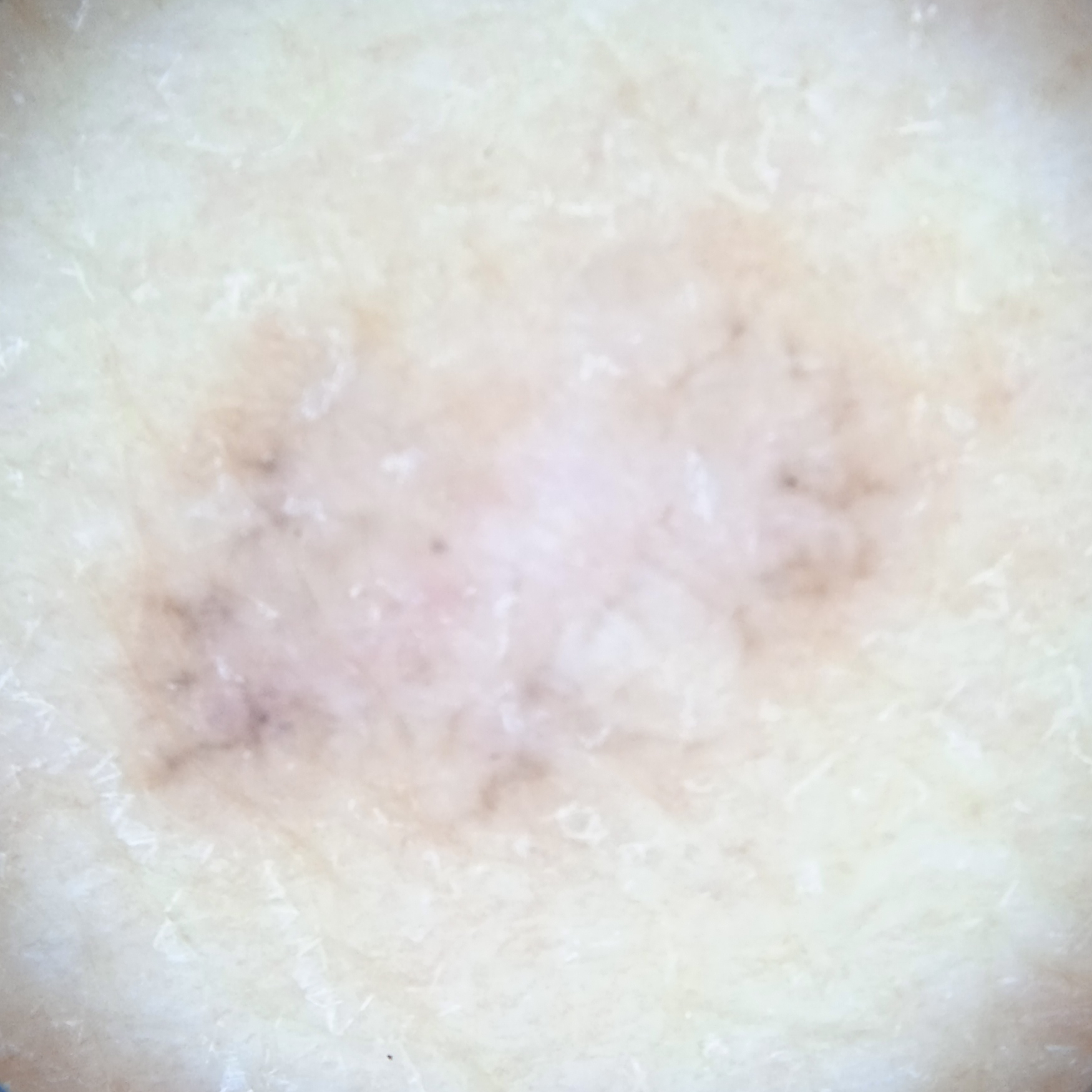{
  "diagnosis": {
    "name": "basal cell carcinoma",
    "malignancy": "malignant"
  }
}